A female subject, approximately 40 years of age · a dermatoscopic image of a skin lesion:
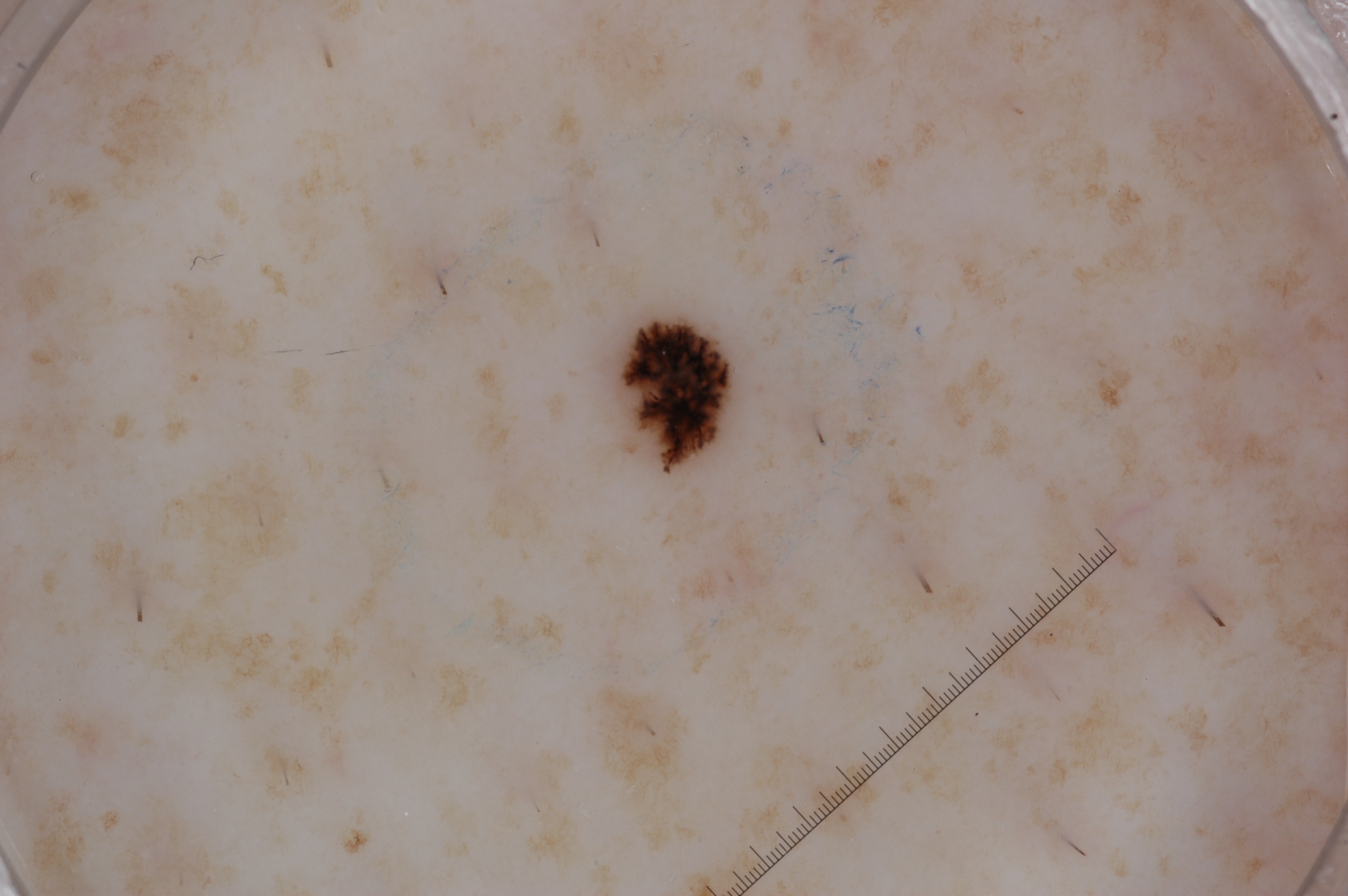lesion bbox = 622, 322, 726, 455; features = streaks and milia-like cysts; assessment = a melanocytic nevus.